A clinical photograph showing a skin lesion in context. Fitzpatrick II. A female patient aged around 85 or older.
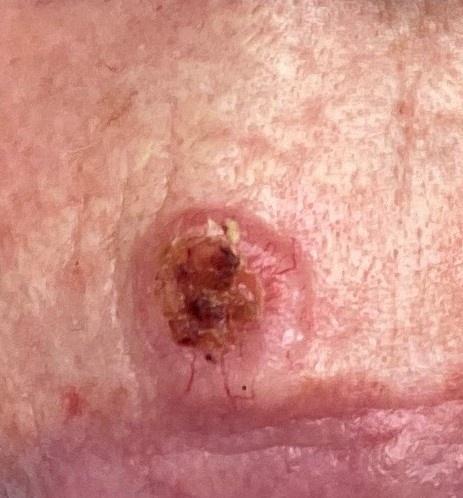Conclusion:
Histopathological examination showed a basal cell carcinoma.